A male subject, aged 58-62. A dermoscopic image of a skin lesion.
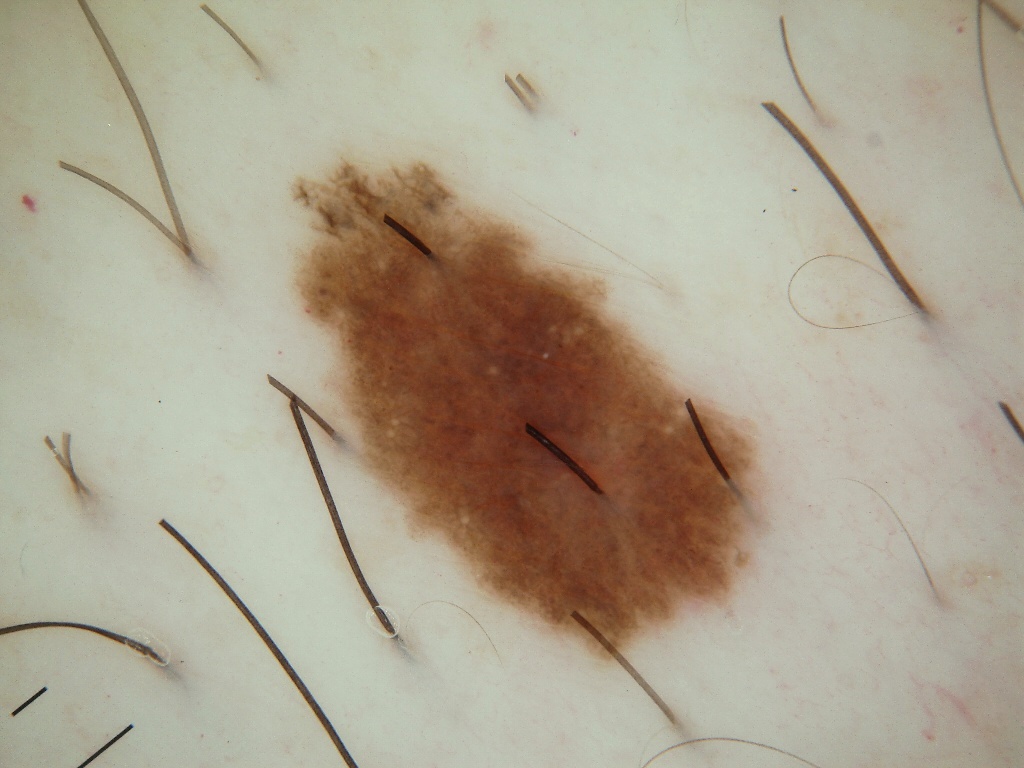The dermoscopic pattern shows globules, pigment network, and milia-like cysts; no negative network or streaks. The lesion occupies the region left=298, top=164, right=759, bottom=659. Clinically diagnosed as a melanocytic nevus, a benign lesion.